A skin lesion imaged with a dermatoscope.
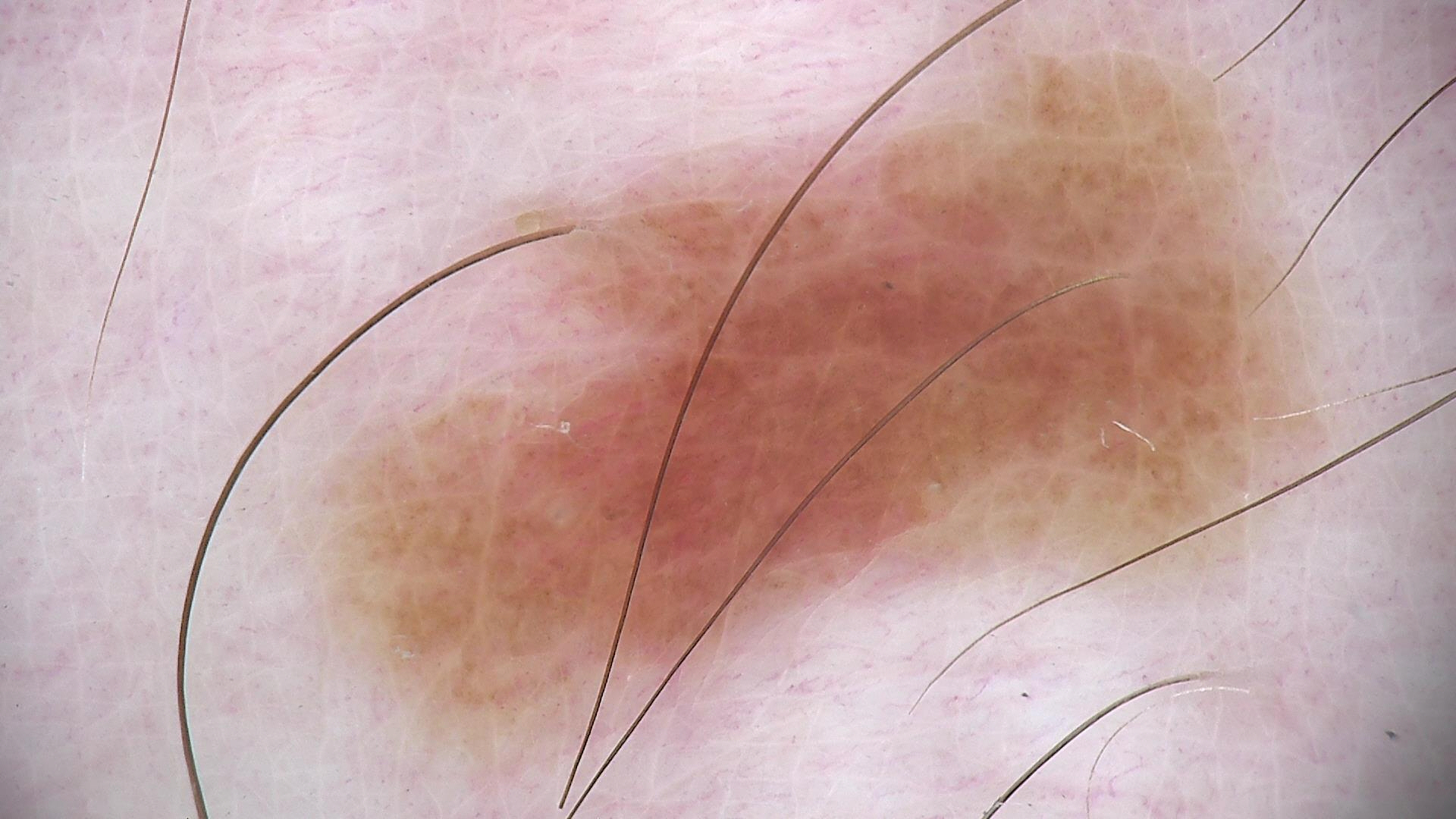| key | value |
|---|---|
| assessment | dysplastic junctional nevus (expert consensus) |